The lesion is described as rough or flaky and raised or bumpy; the patient reports the condition has been present for one to four weeks; the palm is involved; reported lesion symptoms include itching and burning; the patient reported no systemic symptoms; self-categorized by the patient as a rash; this is a close-up image — 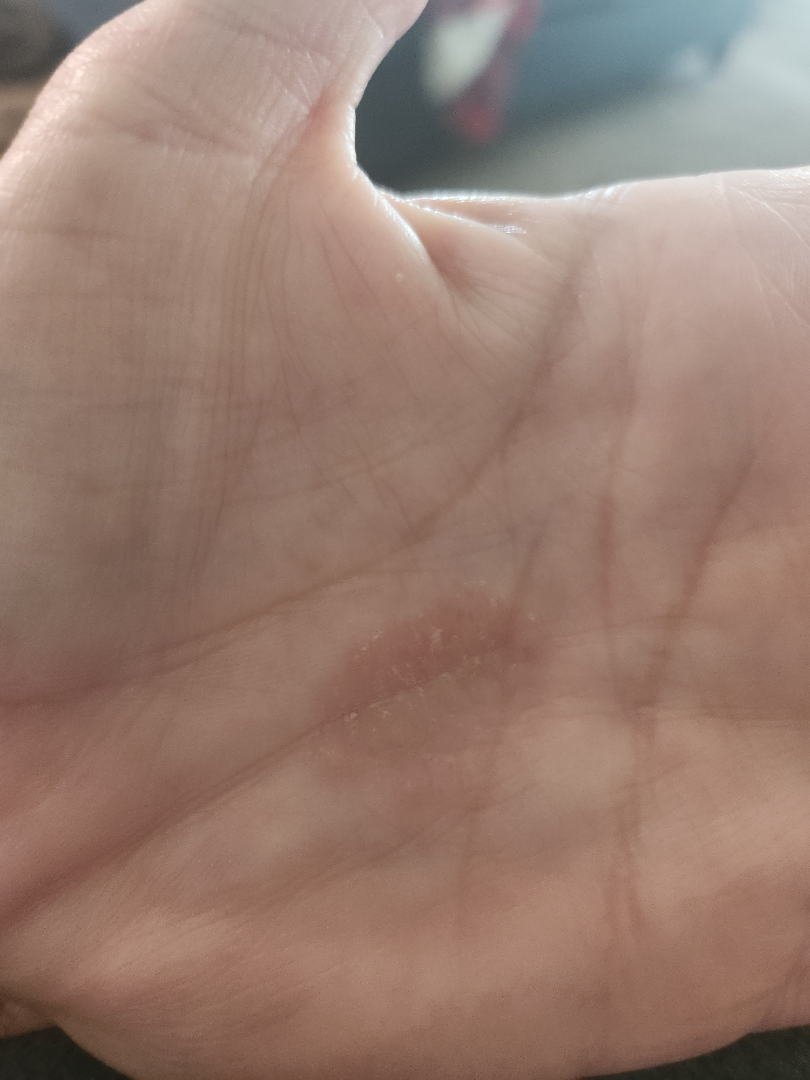Q: What is the dermatologist's impression?
A: Psoriasis (possible); Eczema (possible)